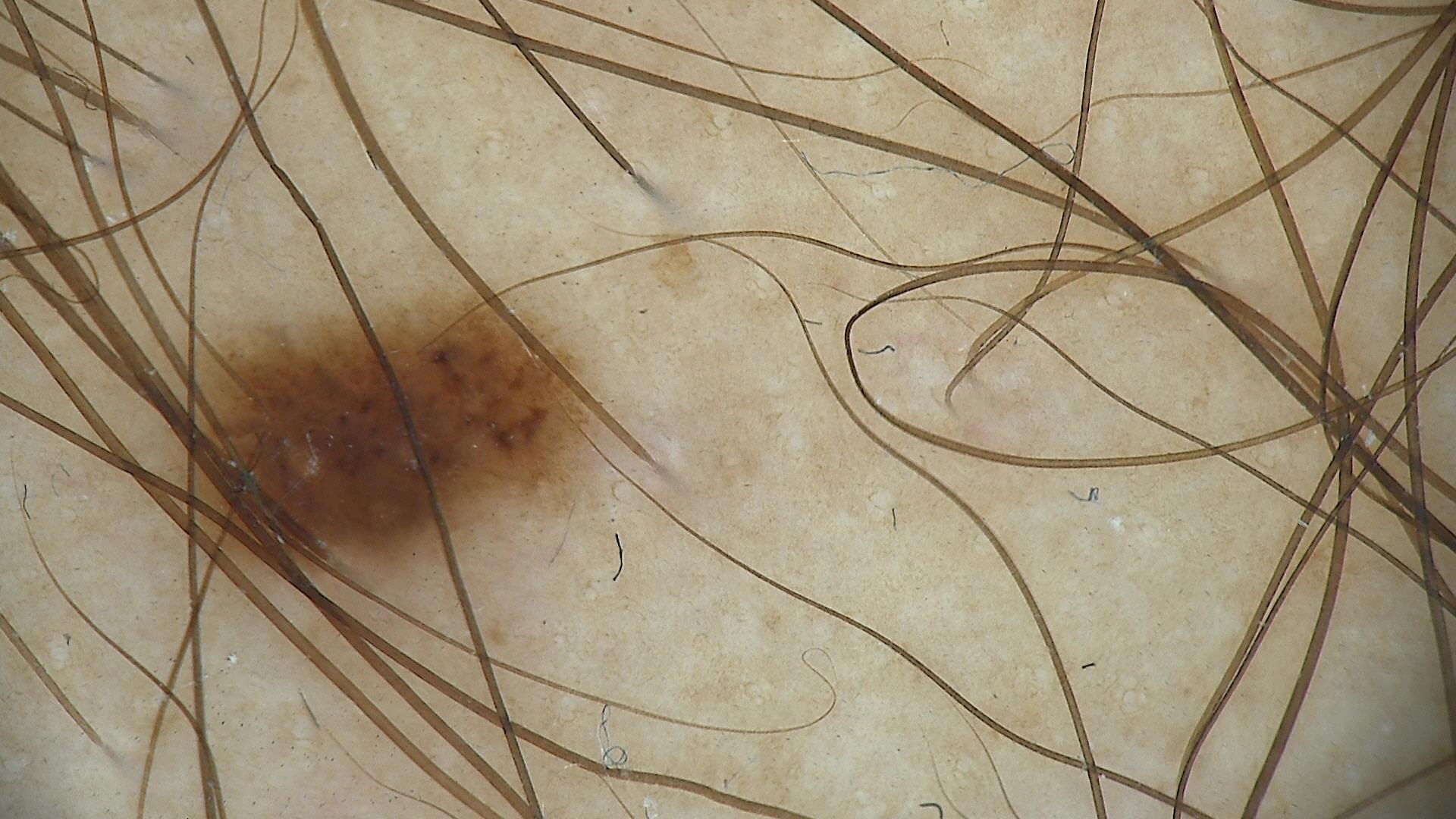modality: dermatoscopy, class: dysplastic junctional nevus (expert consensus).